Reported lesion symptoms include itching; the photograph was taken at an angle; the affected area is the leg and top or side of the foot; self-categorized by the patient as a rash — 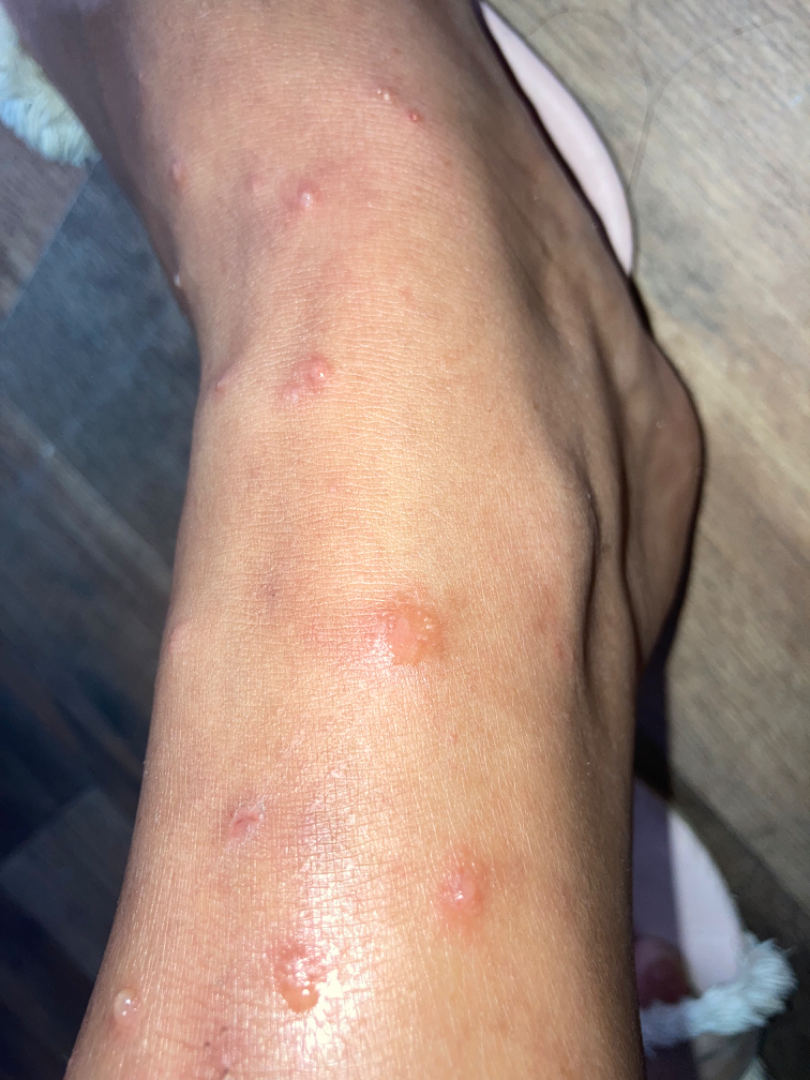differential:
  leading:
    - Insect Bite
  considered:
    - Scabies
    - Allergic Contact Dermatitis